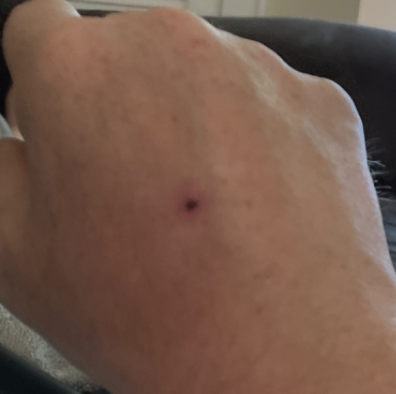assessment=ungradable on photographic review; framing=at a distance; skin tone=lay reviewers estimated MST 2 or 3; anatomic site=back of the hand, leg, head or neck and arm; lesion symptoms=bleeding; surface texture=flat; onset=one to four weeks; subject=male, age 40–49.